A close-up photograph · the patient reported no systemic symptoms · the contributor reports the condition has been present for less than one week · the lesion is described as raised or bumpy, rough or flaky and flat · self-categorized by the patient as a rash · the head or neck is involved · skin tone: Fitzpatrick skin type IV; lay reviewers estimated Monk Skin Tone 2 or 4 (two reviewer pools disagreed) · the lesion is associated with itching and bothersome appearance:
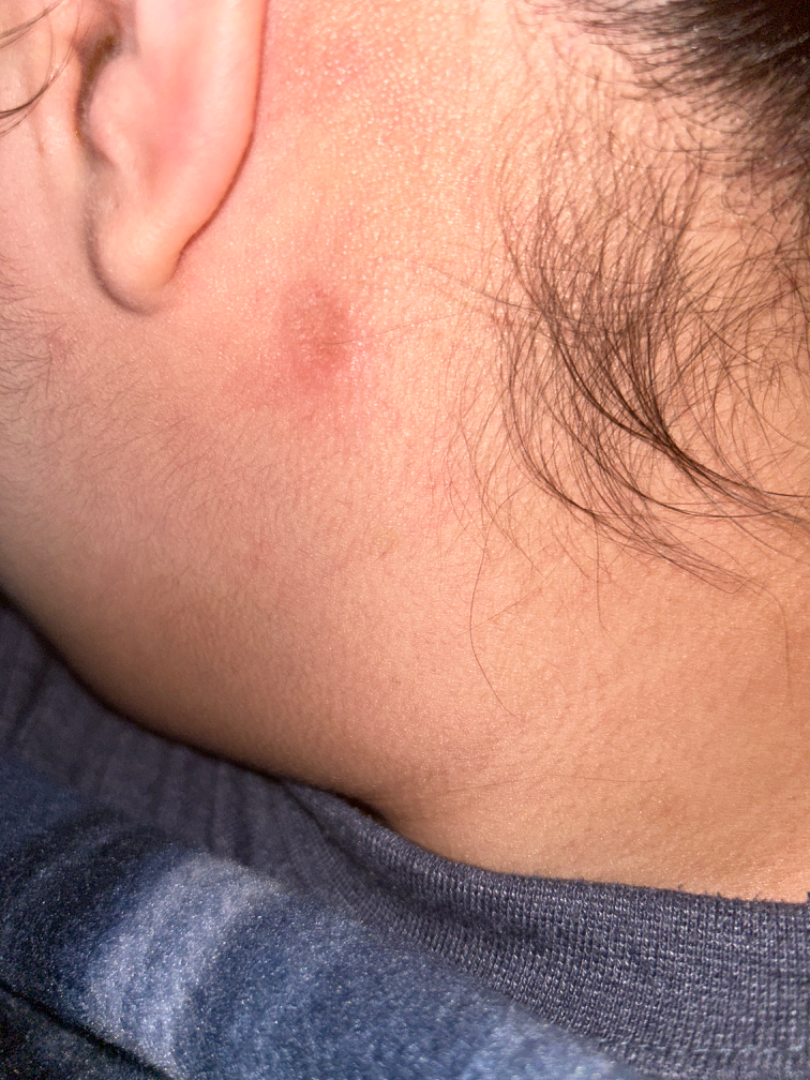Assessment: The case was difficult to assess from the available photograph.